The photograph is a close-up of the affected area:
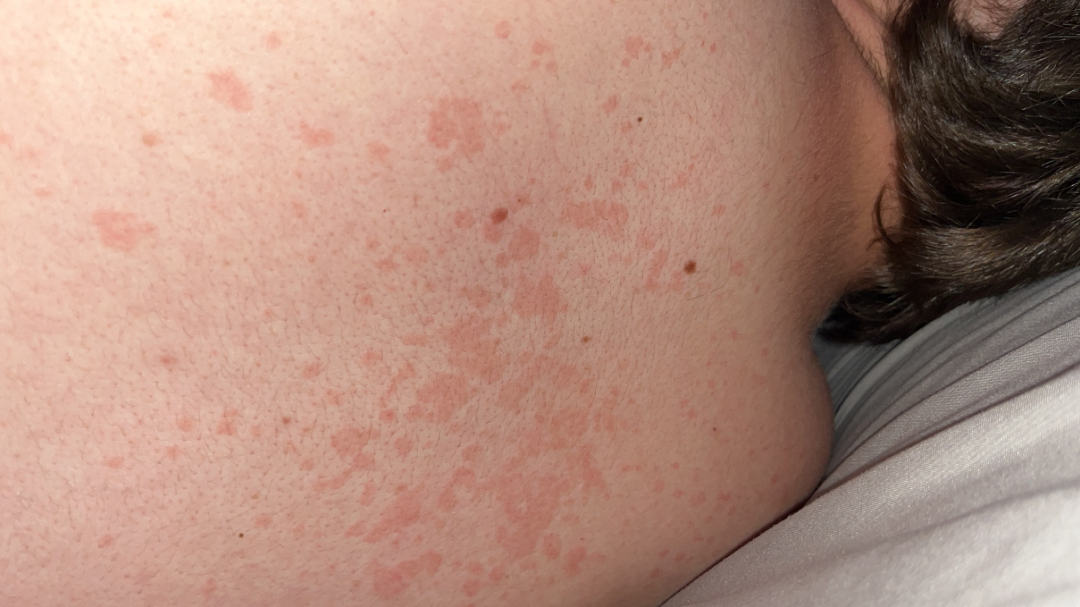clinical impression = Tinea Versicolor (1.00).